A skin lesion imaged with a dermatoscope.
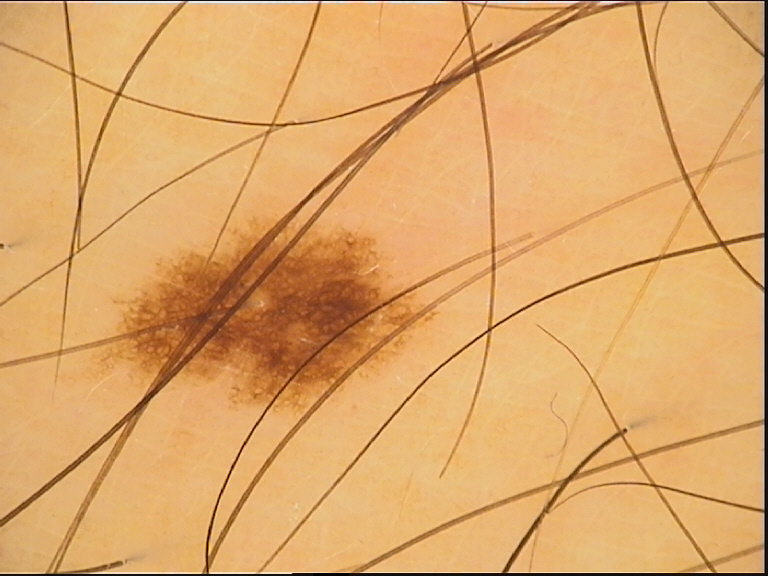Q: What is the diagnosis?
A: junctional nevus (expert consensus)